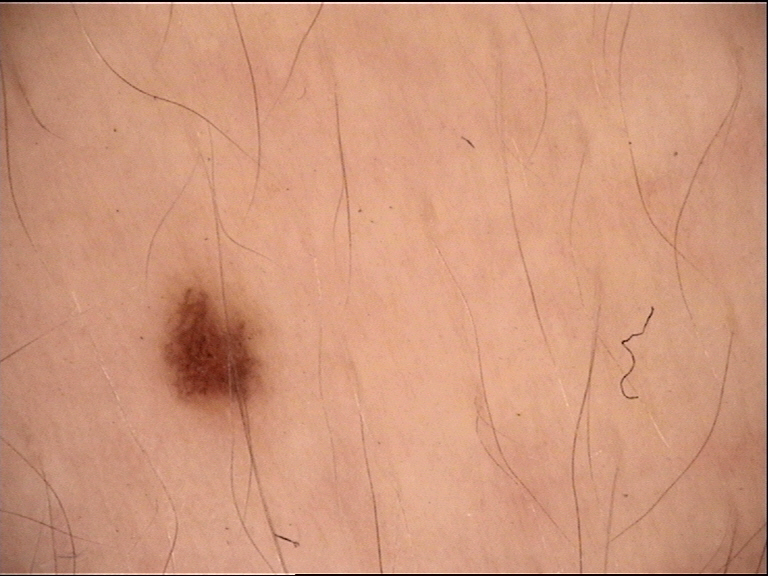diagnosis=dysplastic junctional nevus (expert consensus).